This is a close-up image, the patient reports the condition has been present for one to four weeks, no relevant lesion symptoms reported, located on the leg.
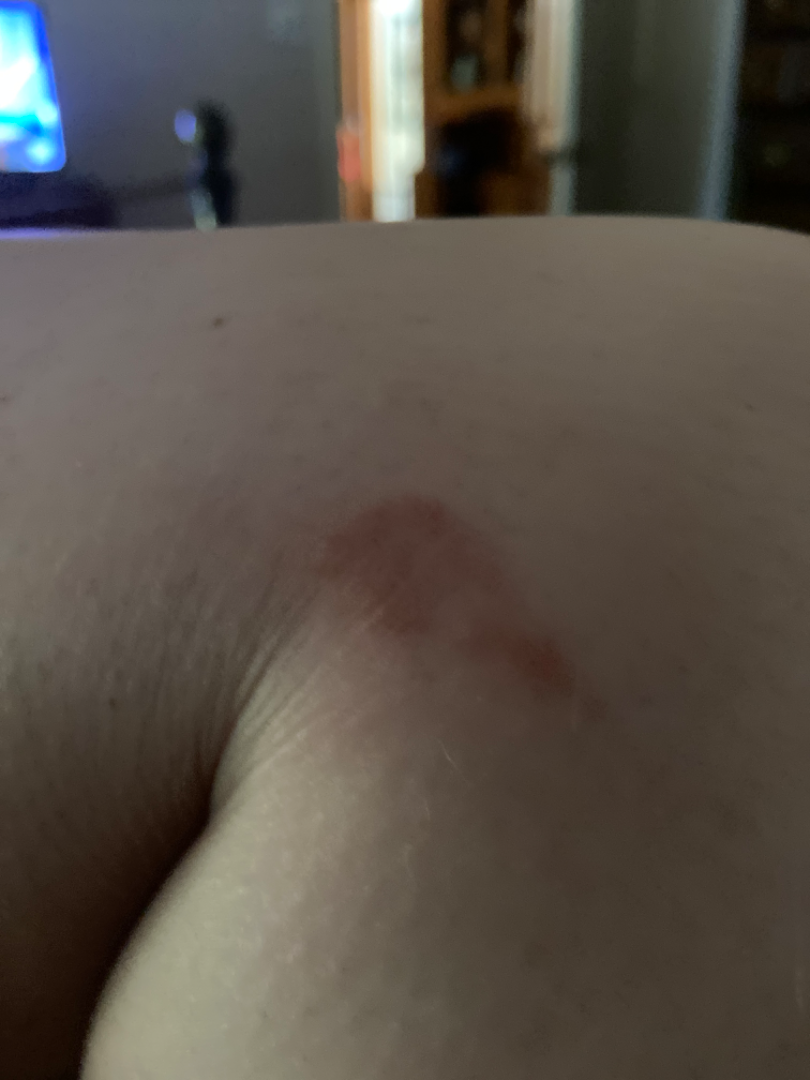  assessment: ungradable on photographic review